A female patient aged approximately 85 or older · contact-polarized dermoscopy of a skin lesion:
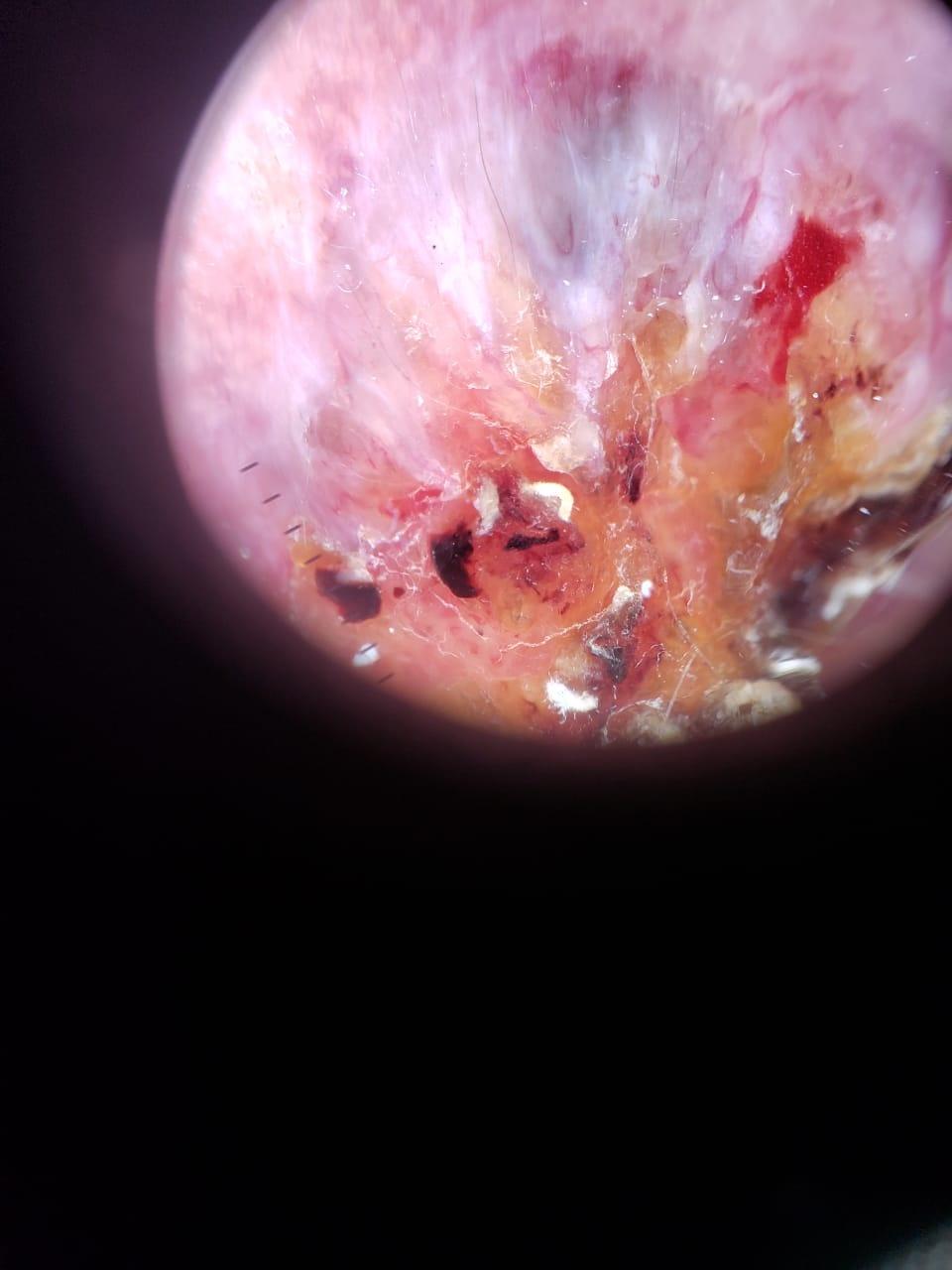Findings: The lesion is located on the head or neck. Pathology: On biopsy, the diagnosis was a squamous cell carcinoma.